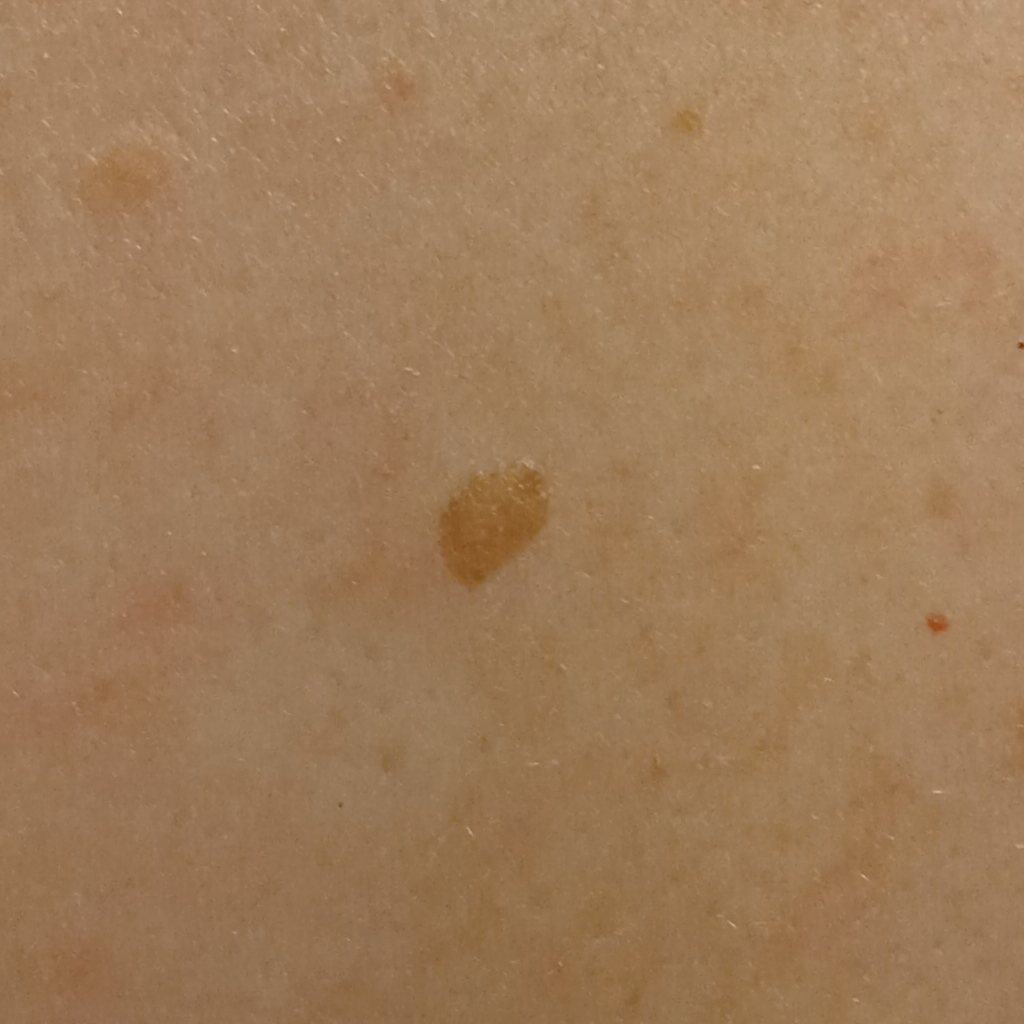Case summary:
The patient describes having numerous moles. A female subject 54 years old. The patient says their skin reddens with sun exposure. Acquired for a research image collection, with no referral diagnosis. On a questionnaire the patient reported a personal history of cancer, a personal history of skin cancer, and a family history of skin cancer. Located on the back. The lesion is about 5.5 mm across.
Conclusion:
The diagnostic impression was a seborrheic keratosis.